The patient described the issue as a rash. Texture is reported as raised or bumpy. The arm and back of the hand are involved. The contributor notes pain, bothersome appearance and itching. This is a close-up image. The subject is 30–39, female. The contributor notes the condition has been present for less than one week: 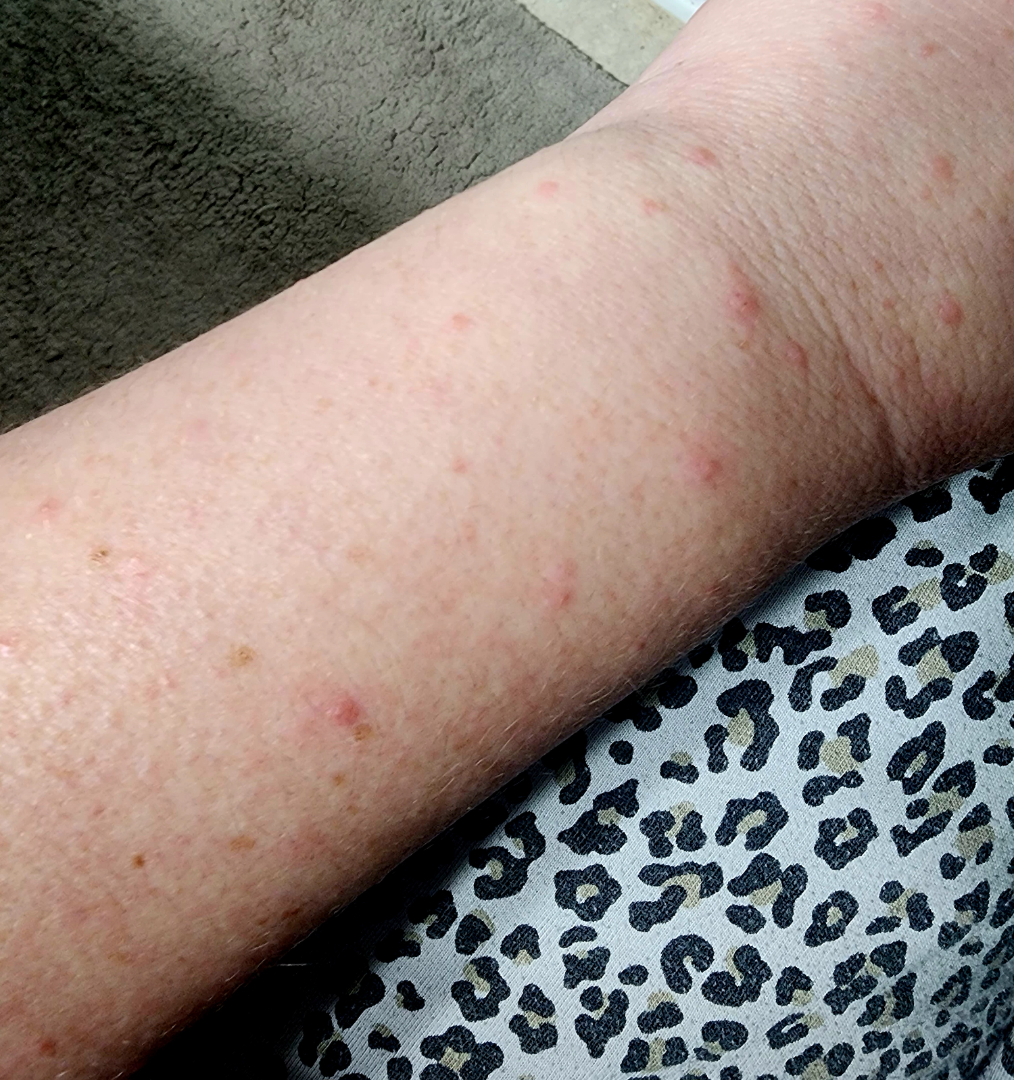Q: What is the dermatologist's impression?
A: the leading impression is Folliculitis; an alternative is Insect Bite